Dermoscopy of a skin lesion.
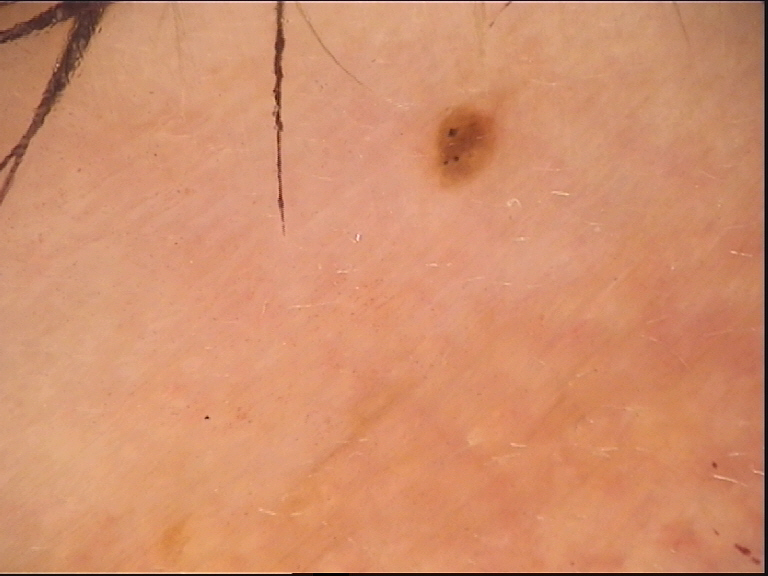Diagnosed as a banal lesion — a compound nevus.